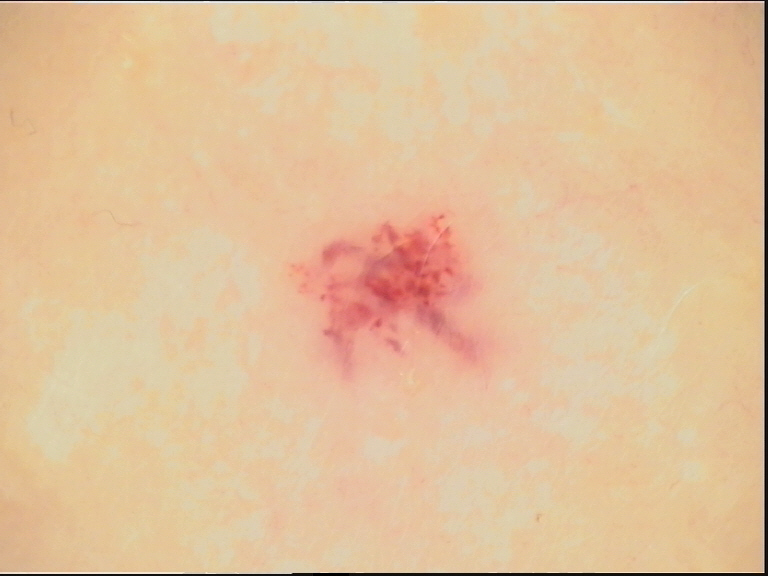Findings:
• image: dermoscopy
• class: hemangioma (expert consensus)